A male patient, roughly 65 years of age · dermoscopy of a skin lesion — 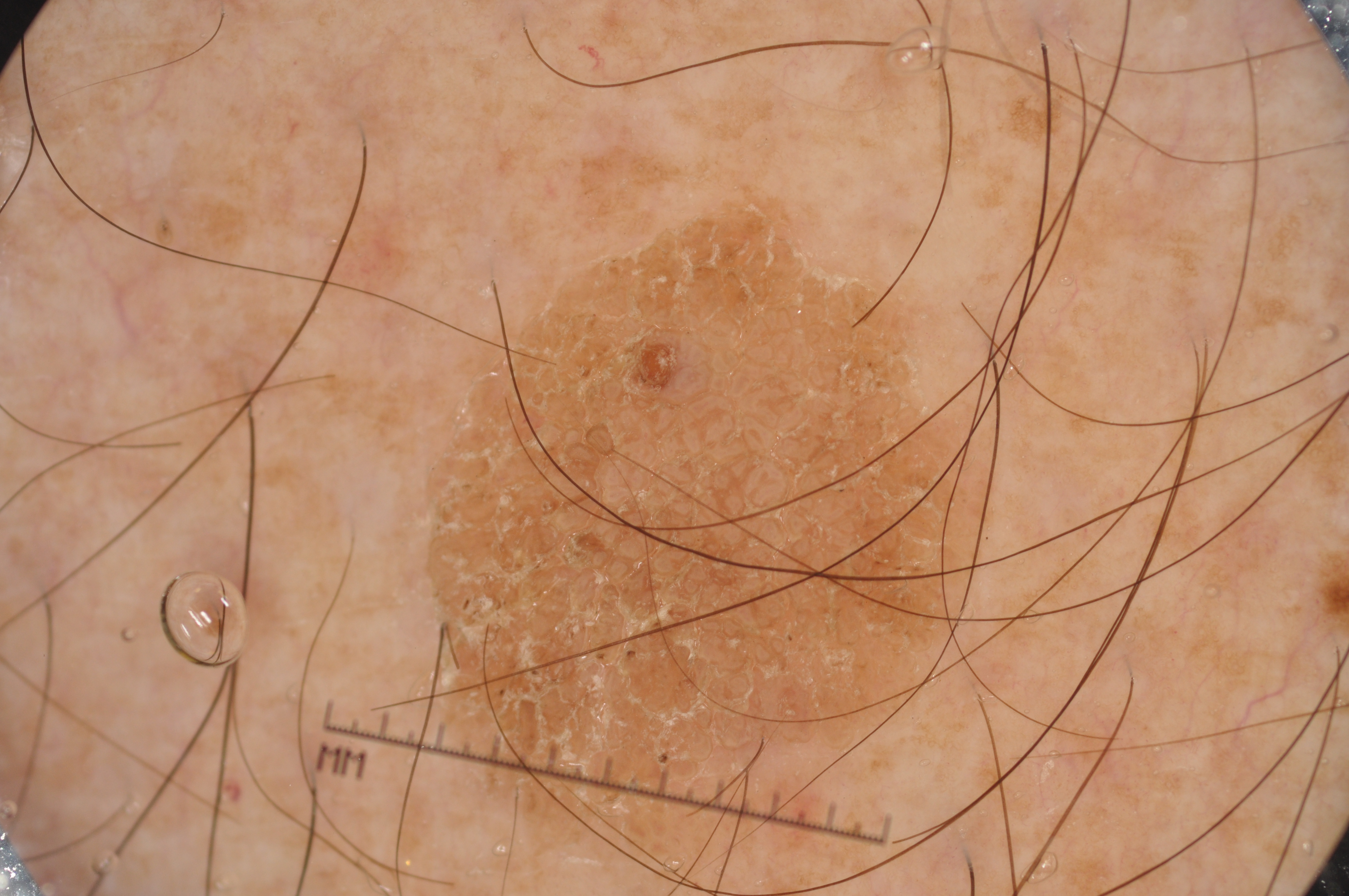location=[393, 188, 1002, 890]
lesion extent=~28% of the field
features=milia-like cysts
assessment=a seborrheic keratosis, a benign lesion